A dermoscopy image of a skin lesion. Few moles overall by the patient's own estimate. A female subject 60 years old. The patient says their skin tans without first burning — 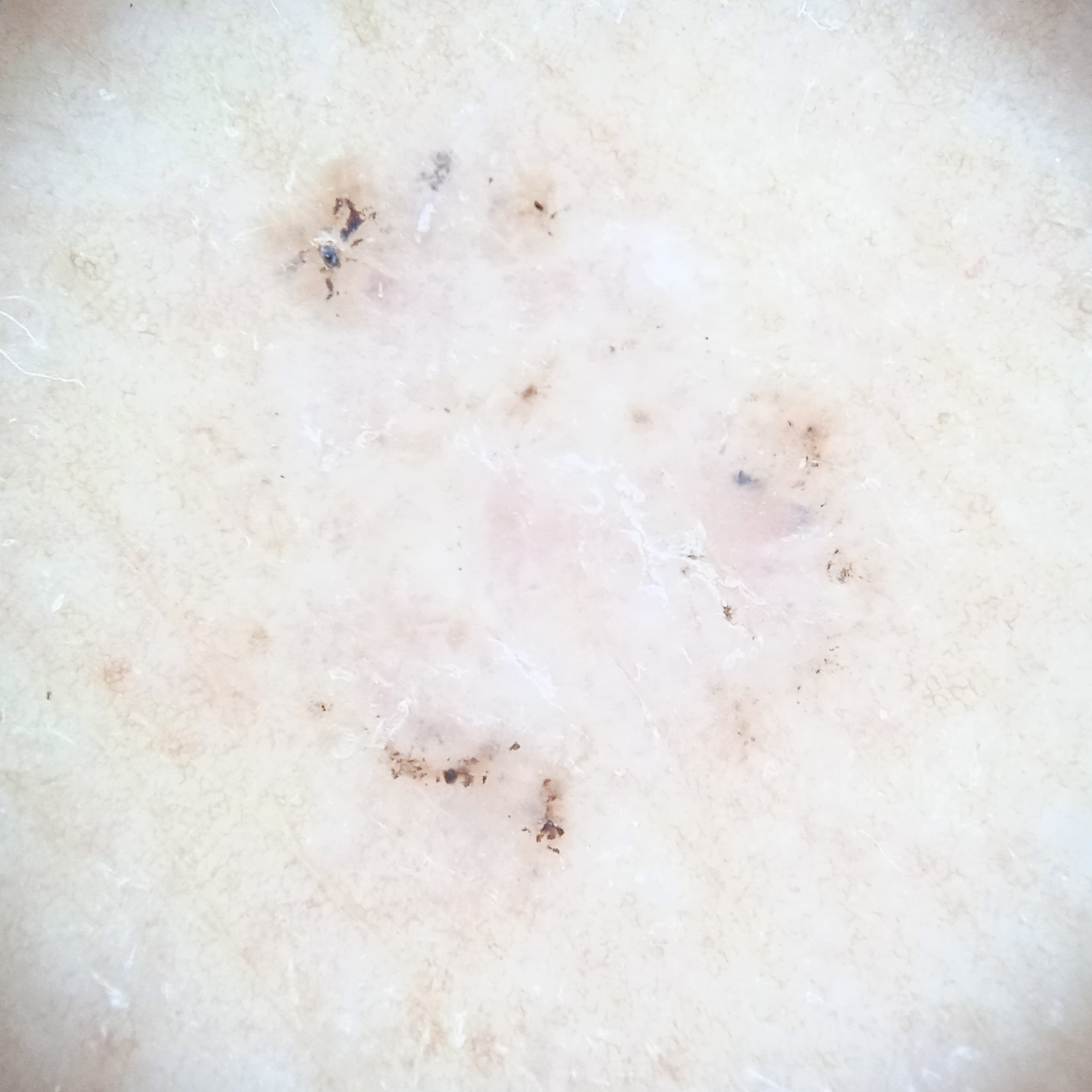Q: What is the anatomic site?
A: the back
Q: Lesion size?
A: 7.8 mm
Q: What was the diagnosis?
A: basal cell carcinoma (dermatologist consensus)